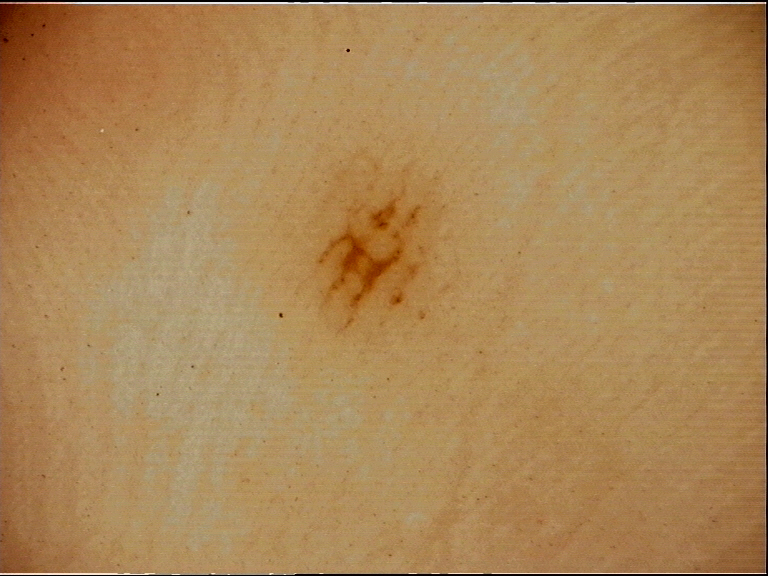Findings:
A dermoscopic close-up of a skin lesion.
Impression:
Diagnosed as an acral dysplastic junctional nevus.